This image was taken at an angle — 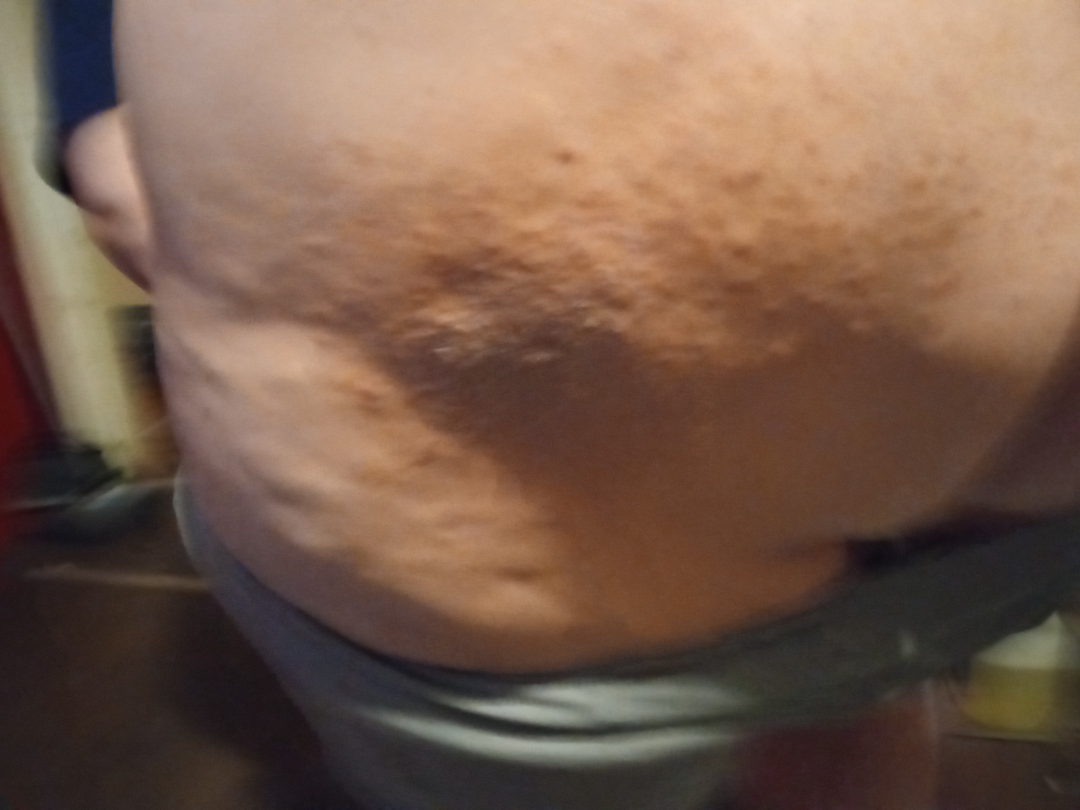Q: What is the dermatologist's impression?
A: the differential includes Psoriasis and Lichen Simplex Chronicus, with no clear leading consideration